Recorded as FST II:
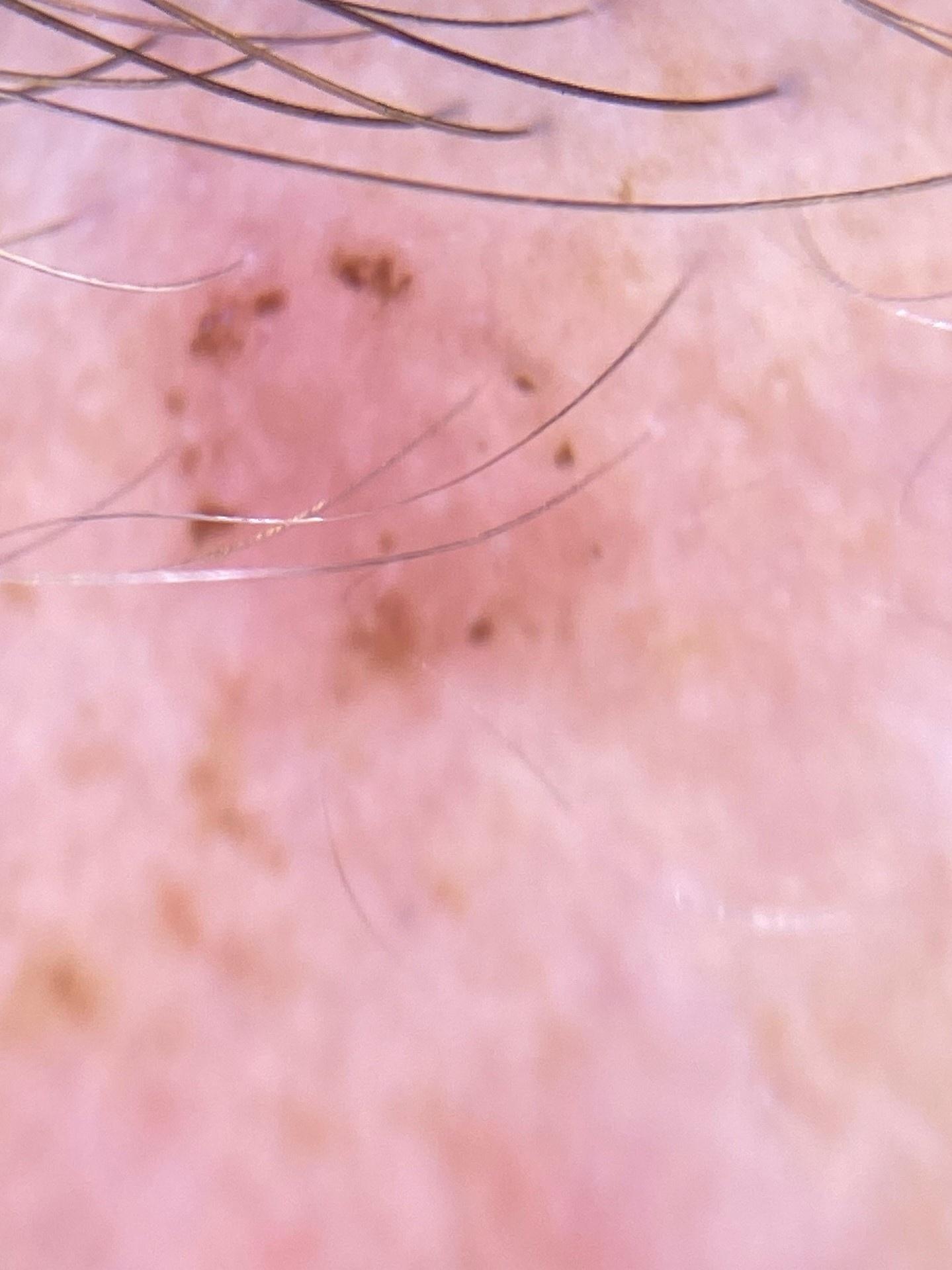location: the head or neck; diagnosis: Basal cell carcinoma (biopsy-proven).